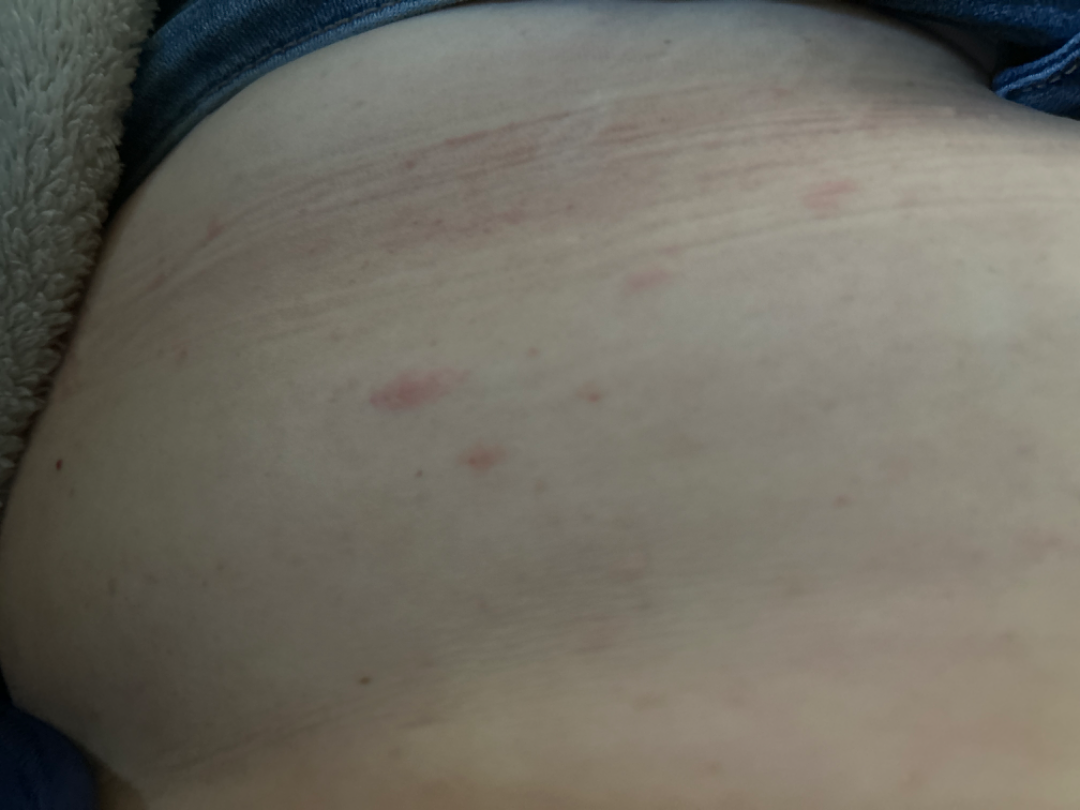The reviewer was unable to grade this case for skin condition. The contributor is a female aged 40–49. Close-up view. The patient considered this a rash. The lesion involves the leg, front of the torso, arm and back of the torso. The condition has been present for about one day. The lesion is described as raised or bumpy.